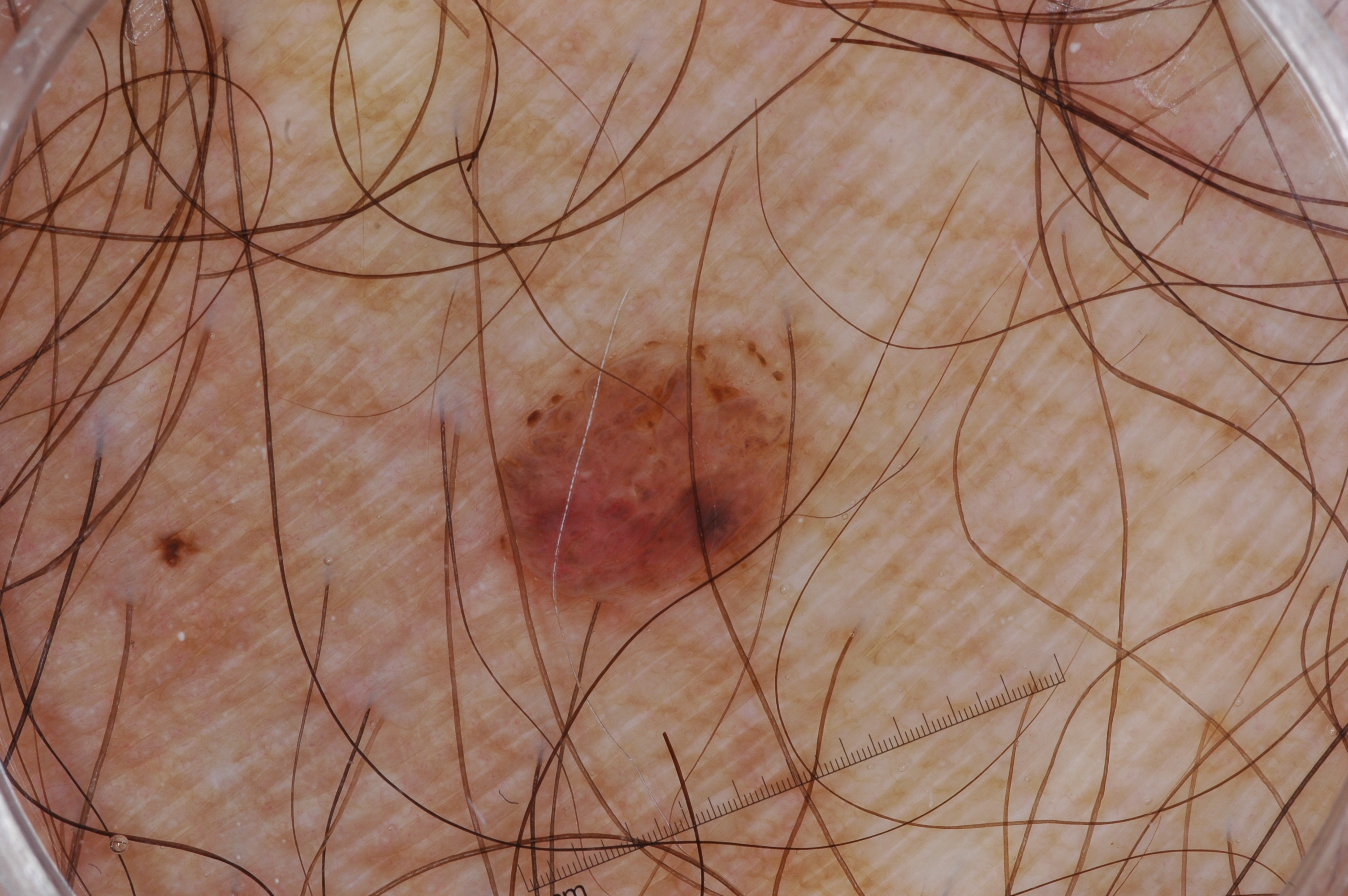  image:
    modality: dermoscopy
  lesion_location:
    bbox_xyxy:
      - 506
      - 336
      - 822
      - 616
  dermoscopic_features:
    present: []
    absent:
      - pigment network
      - streaks
      - negative network
      - milia-like cysts
  lesion_extent: small
  diagnosis:
    name: melanocytic nevus
    malignancy: benign
    lineage: melanocytic
    provenance: clinical